The affected area is the leg, back of the hand and top or side of the foot; the photograph was taken at a distance.
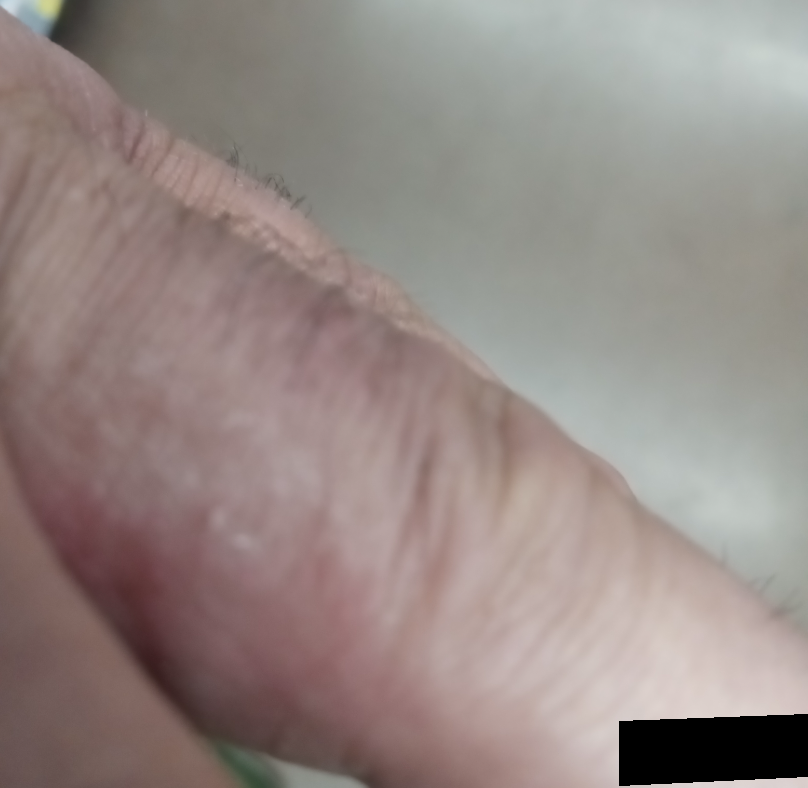No differential diagnosis could be assigned on photographic review.